A female subject aged 35. Imaged for a research study, with no referral diagnosis recorded. A moderate number of moles by the patient's own estimate: 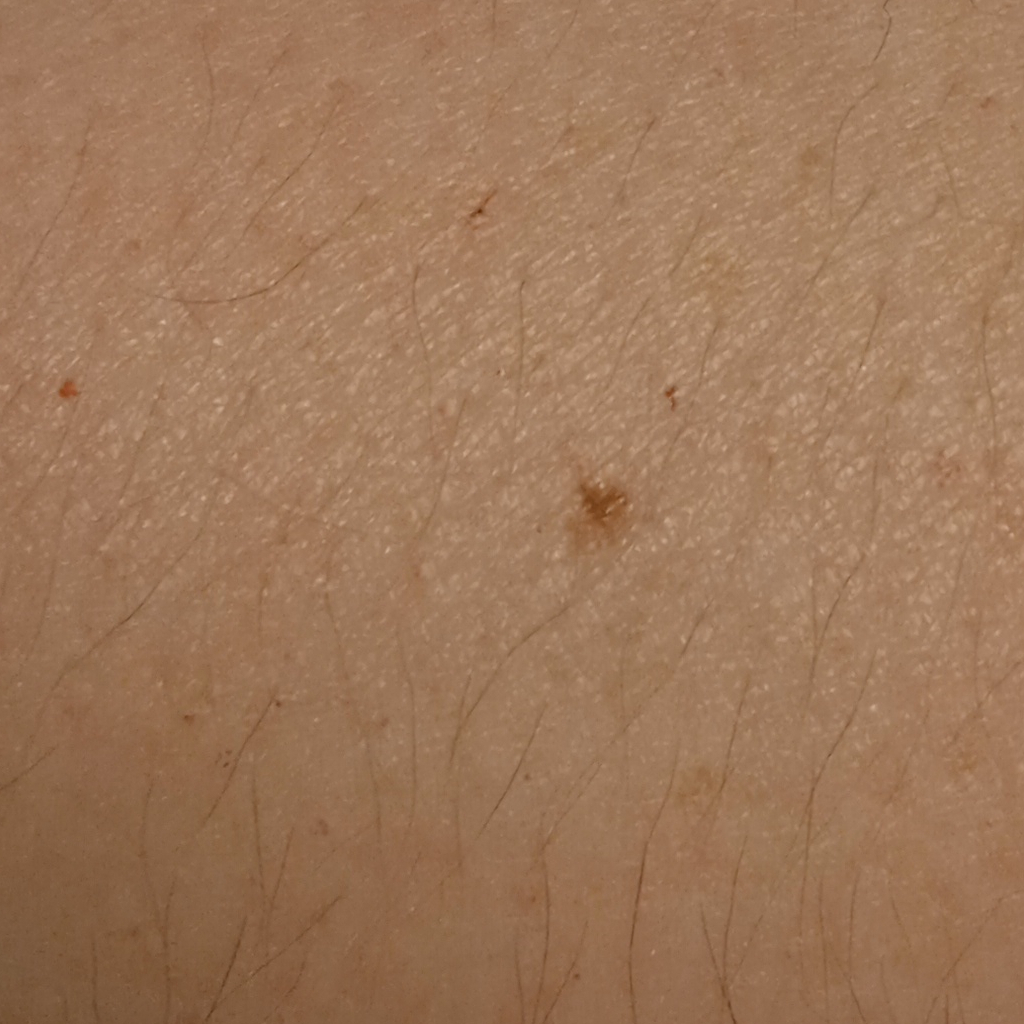The lesion is located on an arm.
The consensus diagnosis for this lesion was a melanocytic nevus.